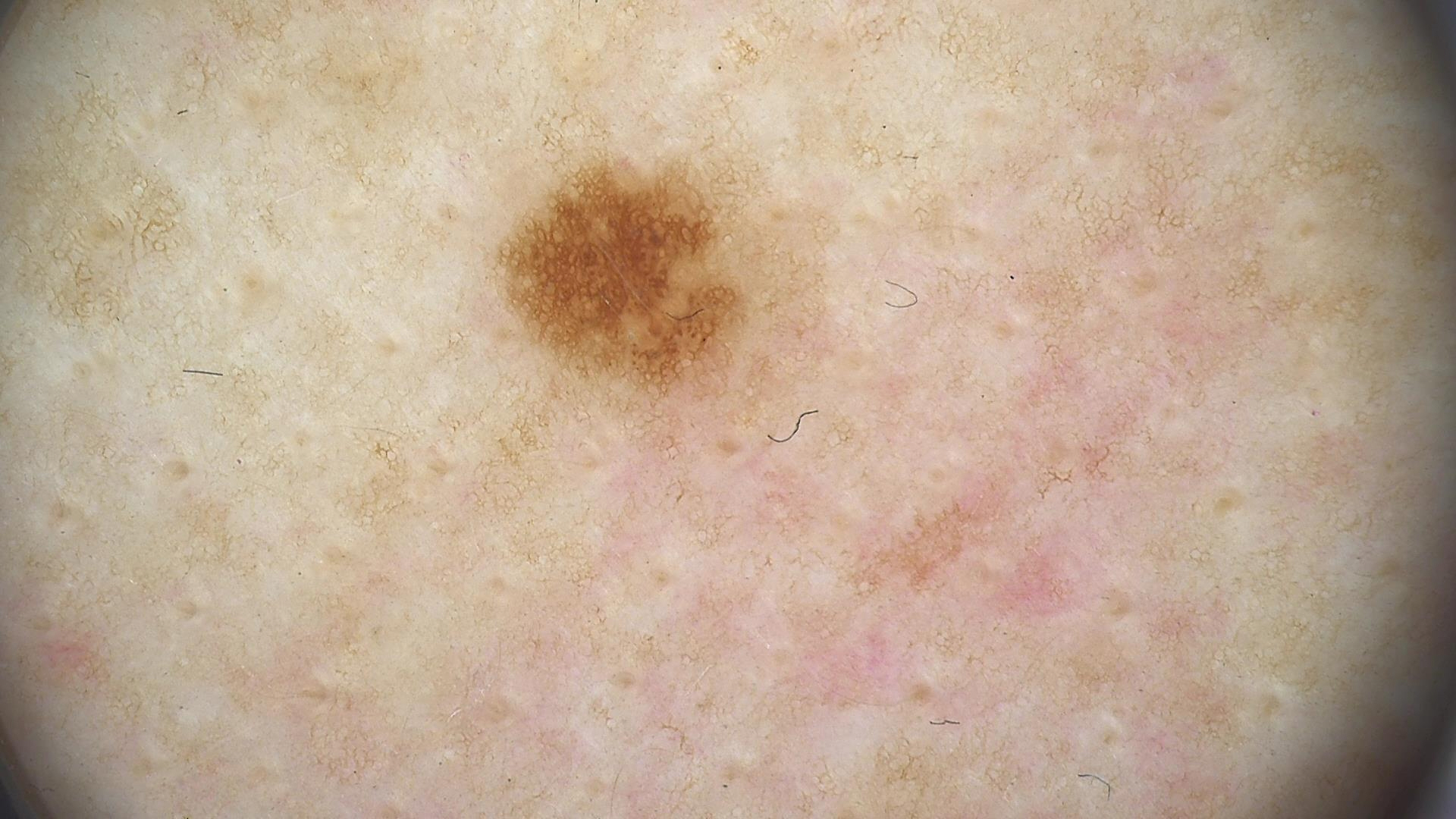A dermoscopic photograph of a skin lesion. The diagnostic label was a benign lesion — a dysplastic junctional nevus.